This image was taken at a distance, the arm is involved, the lesion is associated with bothersome appearance, the contributor reports the lesion is raised or bumpy, the contributor is a male aged 50–59, the patient reported no systemic symptoms, the contributor reports the condition has been present for less than one week:
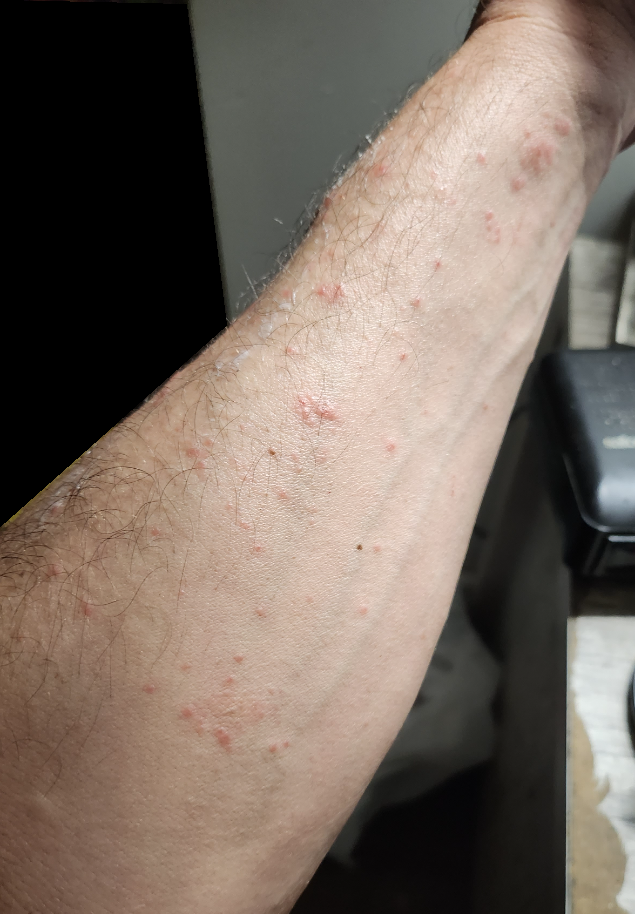• clinical impression: most likely Allergic Contact Dermatitis; with consideration of Scabies; also raised was Insect Bite